This is a close-up image, the affected area is the arm, the contributor reports the condition has been present for about one day: 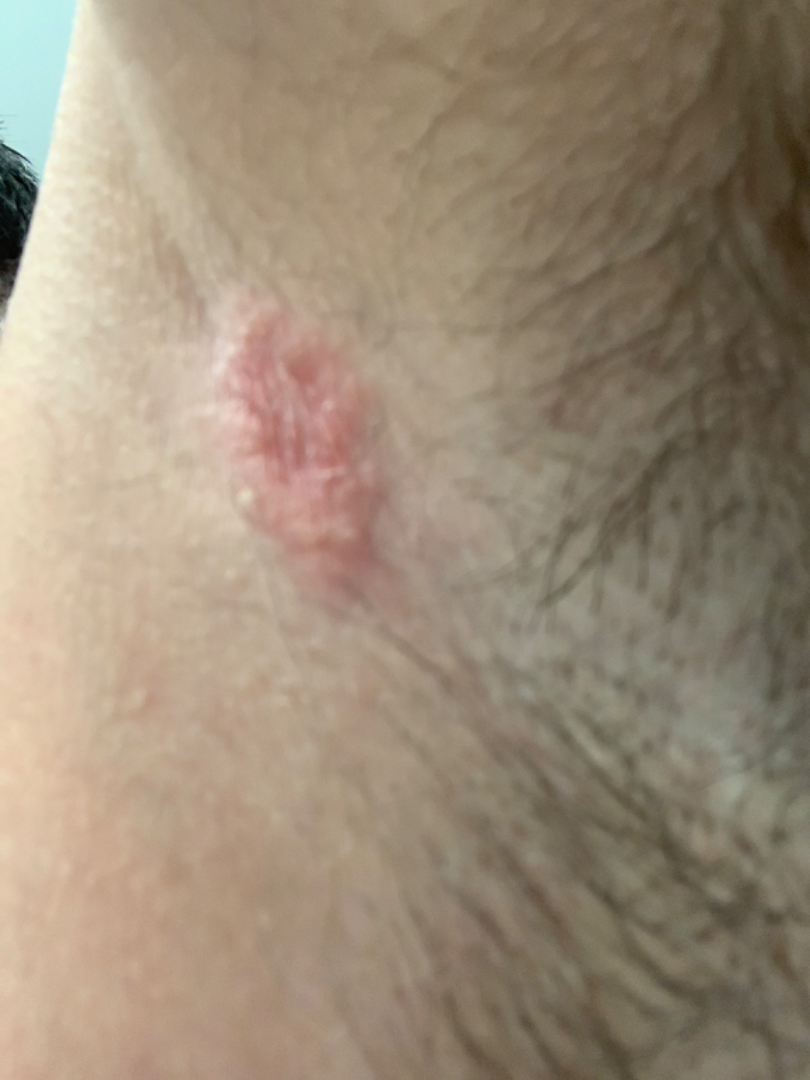assessment: could not be assessed